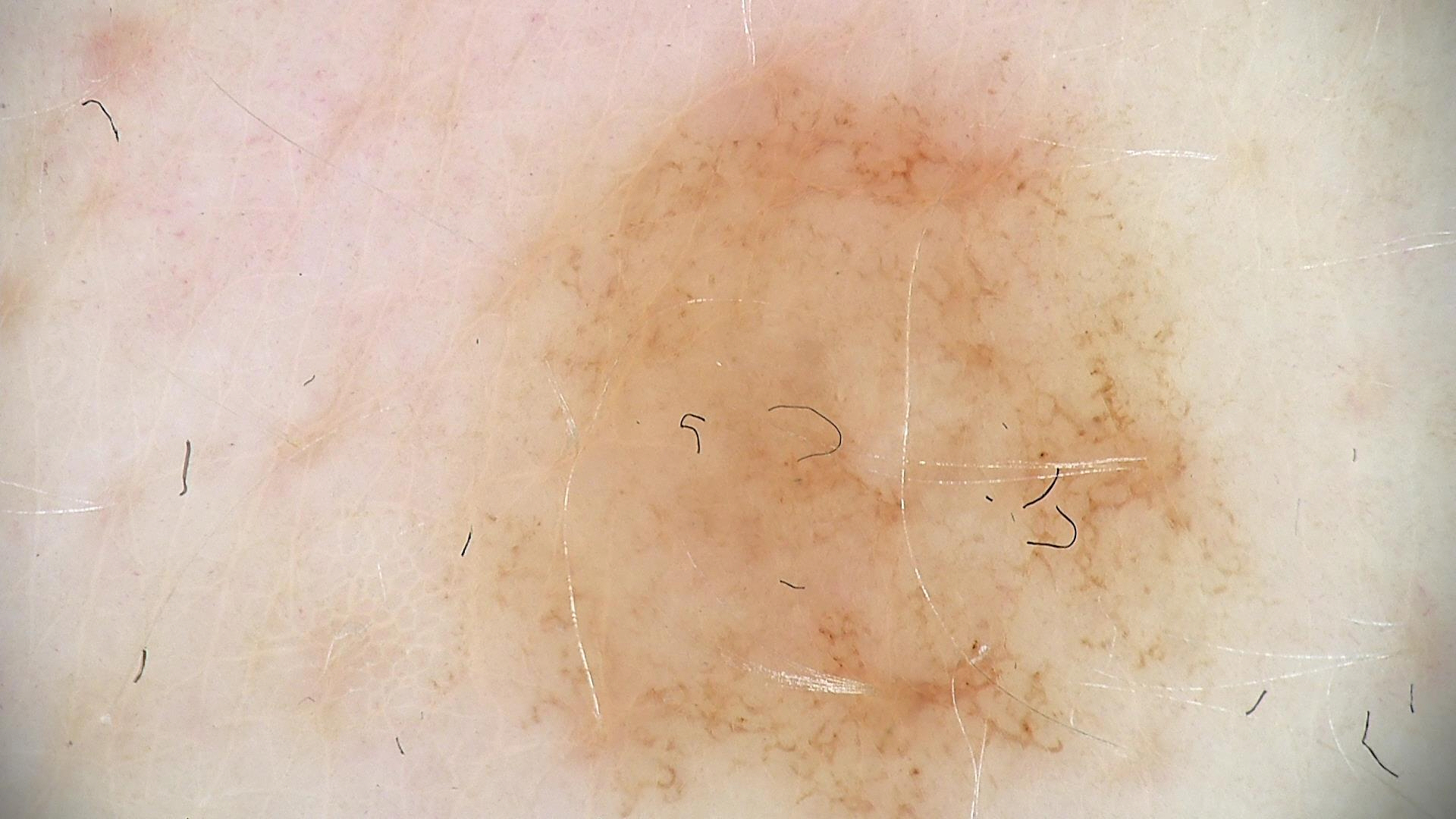Labeled as a dysplastic junctional nevus.